Dermoscopy of a skin lesion.
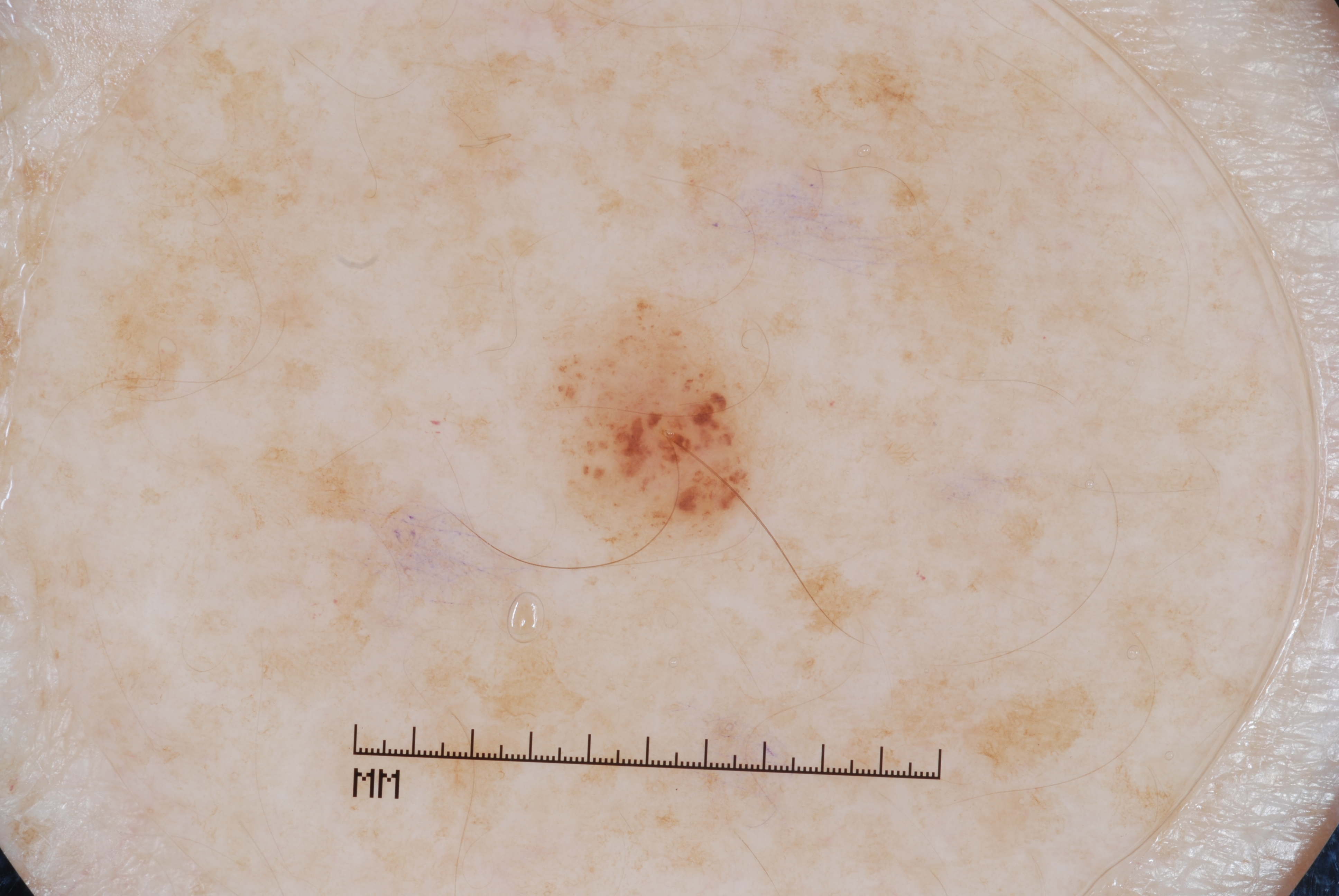Findings: In (x1, y1, x2, y2) order, the lesion occupies the region (555, 301, 753, 539). Impression: The diagnostic assessment was a melanocytic nevus.